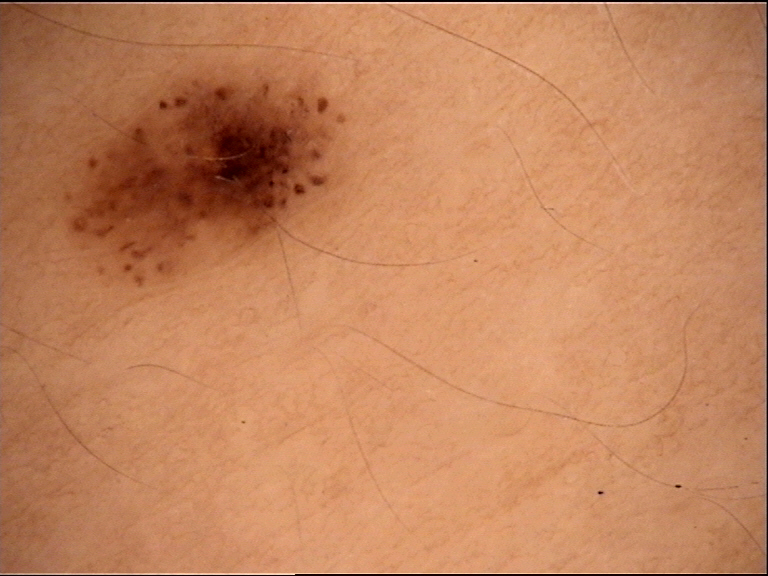A dermatoscopic image of a skin lesion.
Classified as a dysplastic junctional nevus.